A dermatoscopic image of a skin lesion.
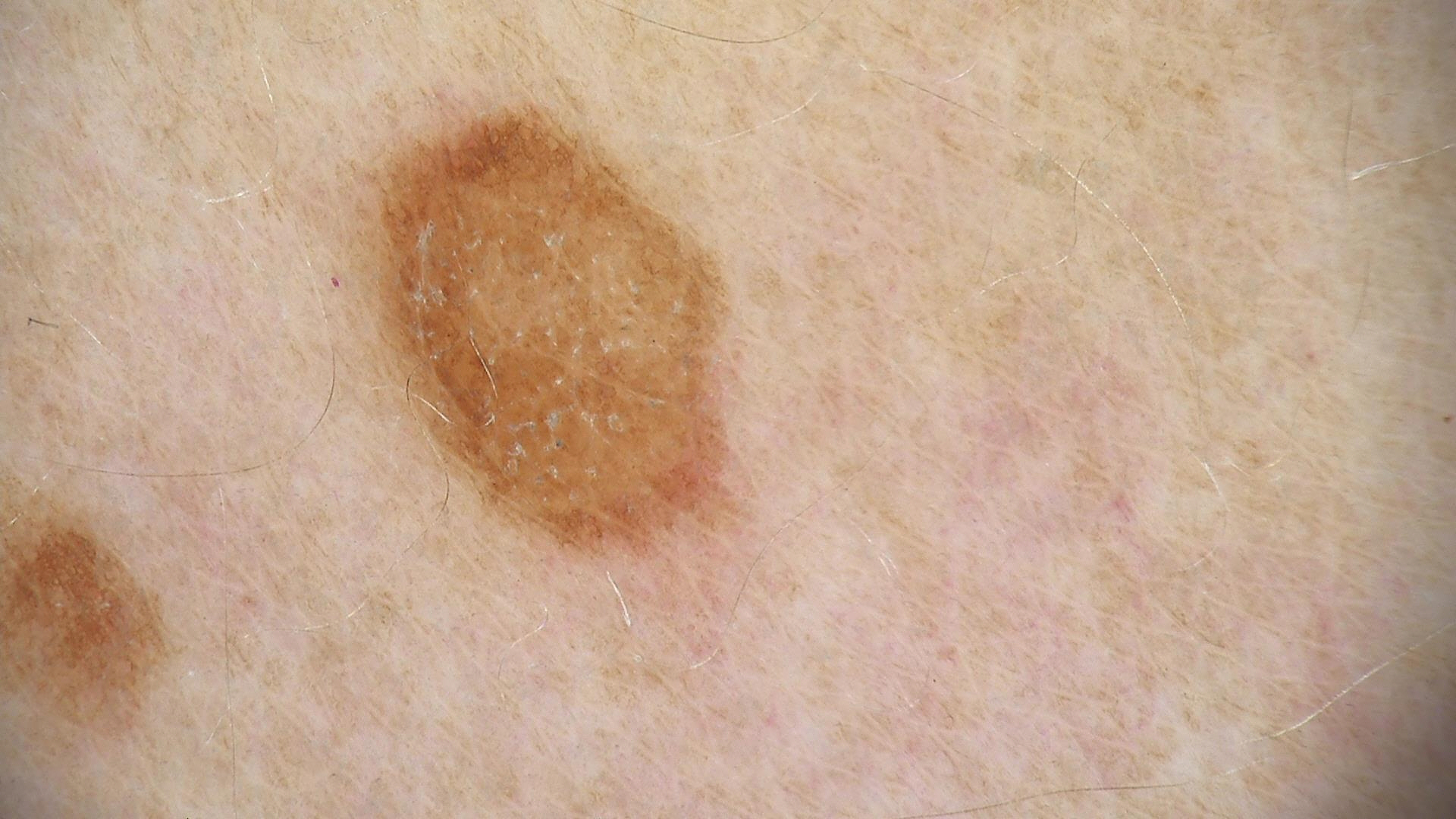The diagnosis was a dysplastic junctional nevus.